The contributor is a female aged 18–29 · this is a close-up image · the lesion involves the head or neck: 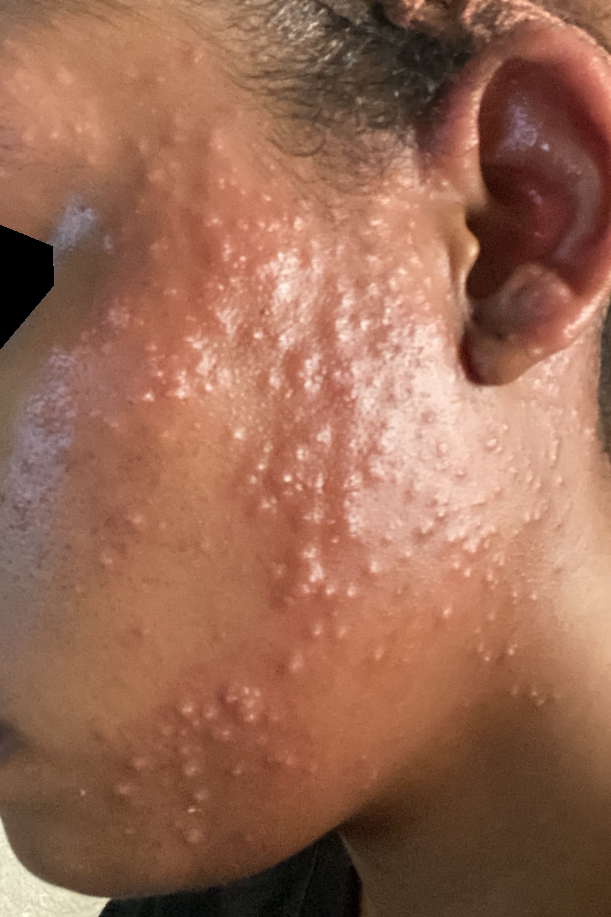assessment — ungradable on photographic review.